The lesion is associated with itching · the patient is 50–59, male · the contributor reports the condition has been present for one to four weeks · the patient reported no systemic symptoms · the patient described the issue as a rash · the arm is involved · texture is reported as raised or bumpy · this image was taken at a distance — 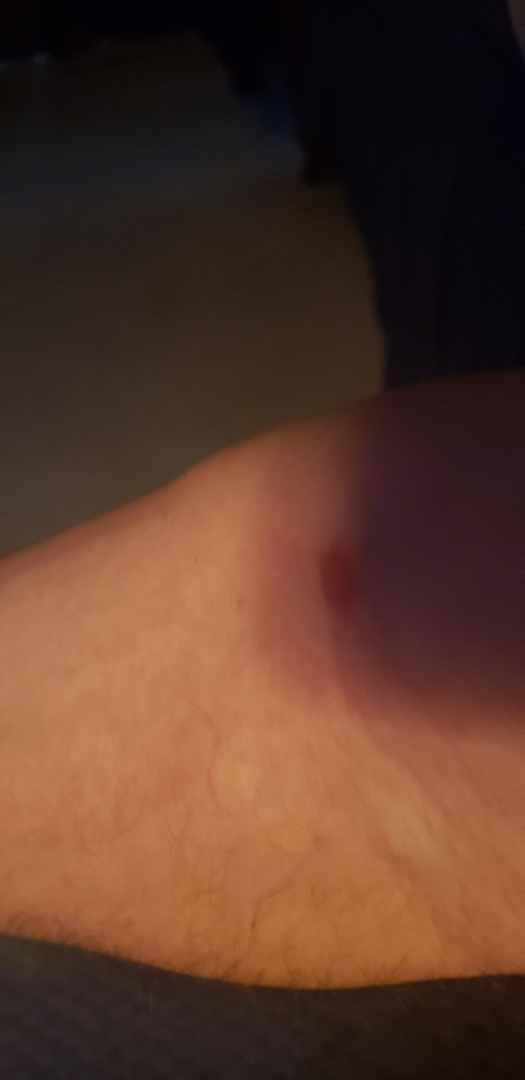| field | value |
|---|---|
| assessment | could not be assessed |